Located on the leg, back of the torso, arm and front of the torso. Reported lesion symptoms include enlargement, burning and itching. The contributor reports the condition has been present for about one day. The photo was captured at an angle. The patient reported no systemic symptoms. The patient is 18–29, female — 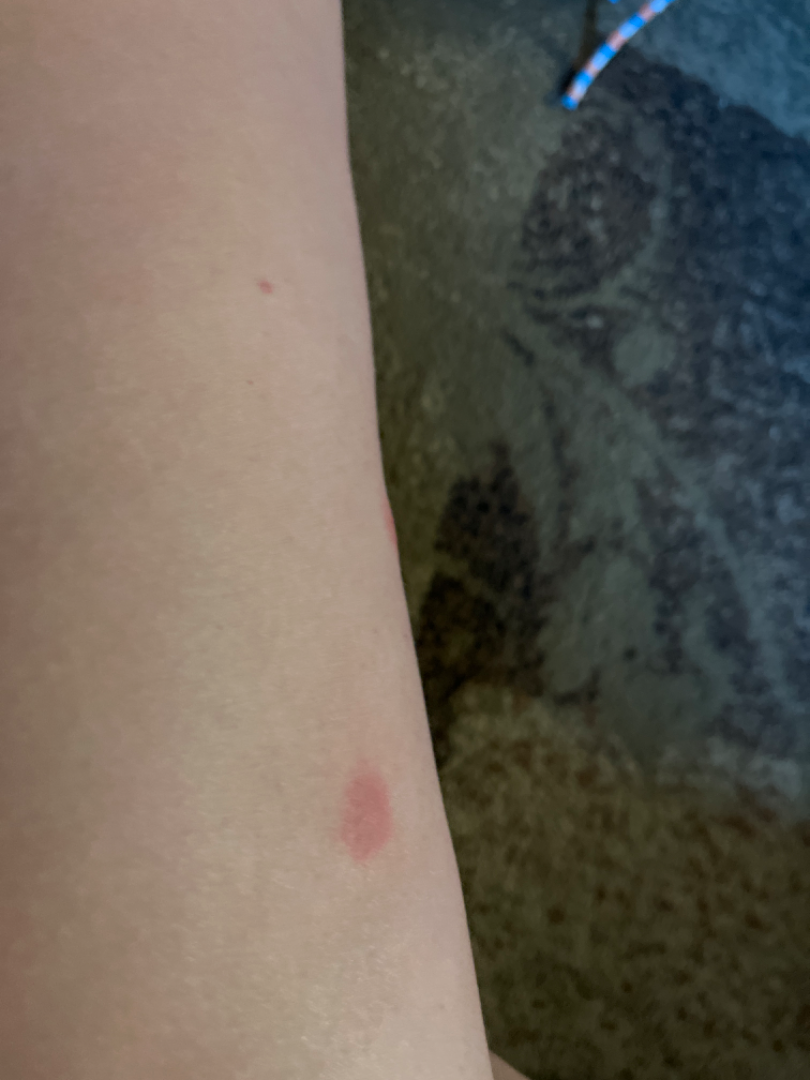Impression: The reviewing dermatologist was unable to assign a differential diagnosis from the image.